The affected area is the back of the hand · the patient considered this a rash · present for less than one week · texture is reported as raised or bumpy · no relevant systemic symptoms · a close-up photograph: 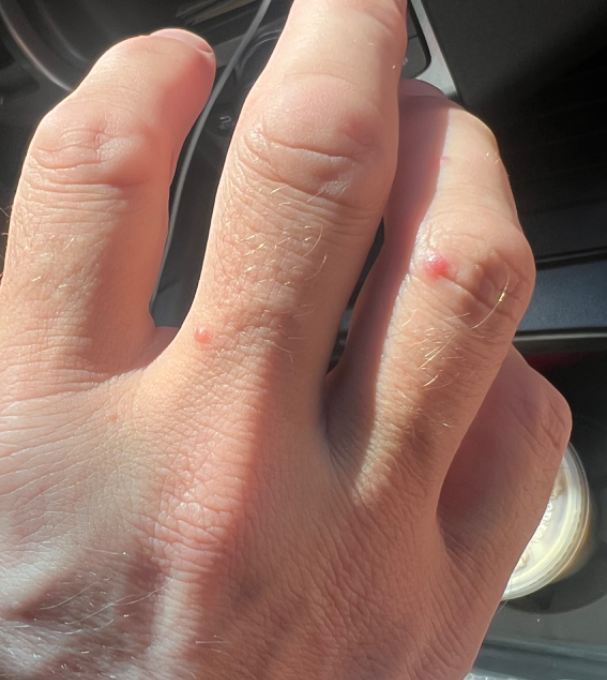The skin condition could not be confidently assessed from this image.